The photograph is a close-up of the affected area · skin tone: human graders estimated Monk skin tone scale 3 · reported duration is about one day · symptoms reported: itching, pain, enlargement and burning · the lesion involves the palm and back of the hand · the patient reported no systemic symptoms · male contributor, age 18–29 · the lesion is described as raised or bumpy and rough or flaky · the patient described the issue as a rash.
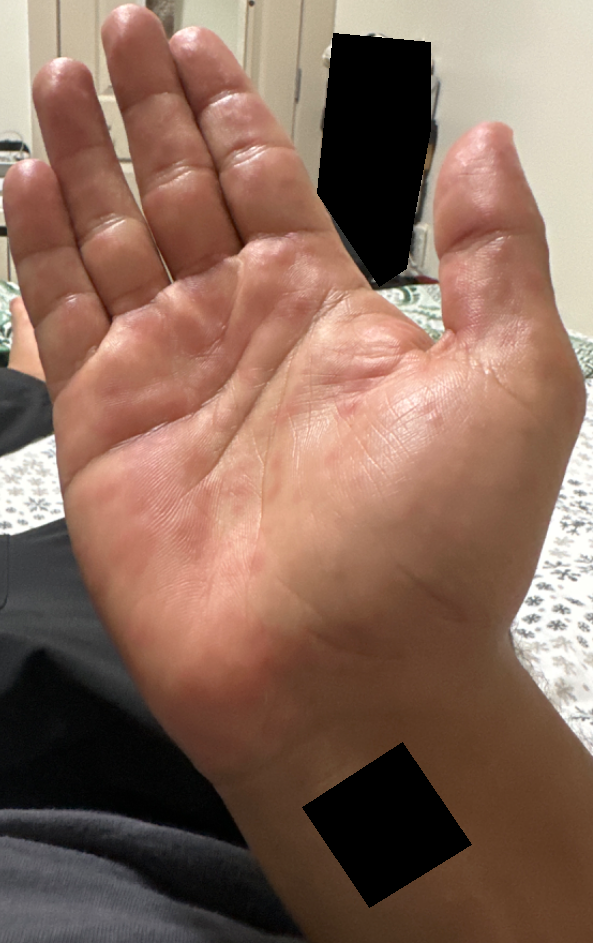differential diagnosis: favoring Eczema; a more distant consideration is Allergic Contact Dermatitis; less probable is Viral Exanthem.